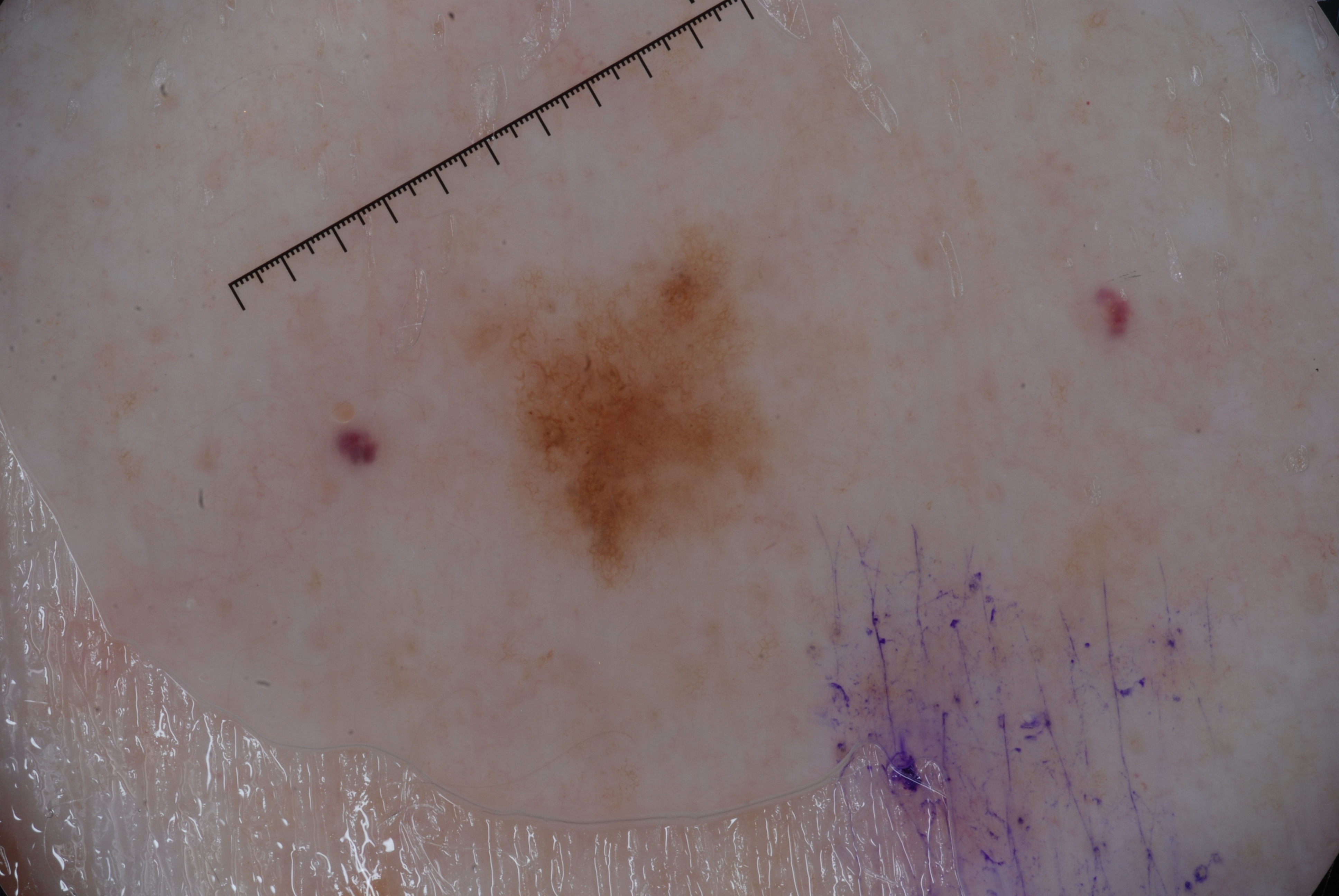Dermoscopy of a skin lesion. In (x1, y1, x2, y2) order, the lesion spans 471/245/774/574. A small lesion within a wider field of skin. Dermoscopy demonstrates pigment network and milia-like cysts; no streaks or negative network. The diagnostic assessment was a melanocytic nevus, a benign skin lesion.